A male subject aged 78 · a dermatoscopic image of a skin lesion — 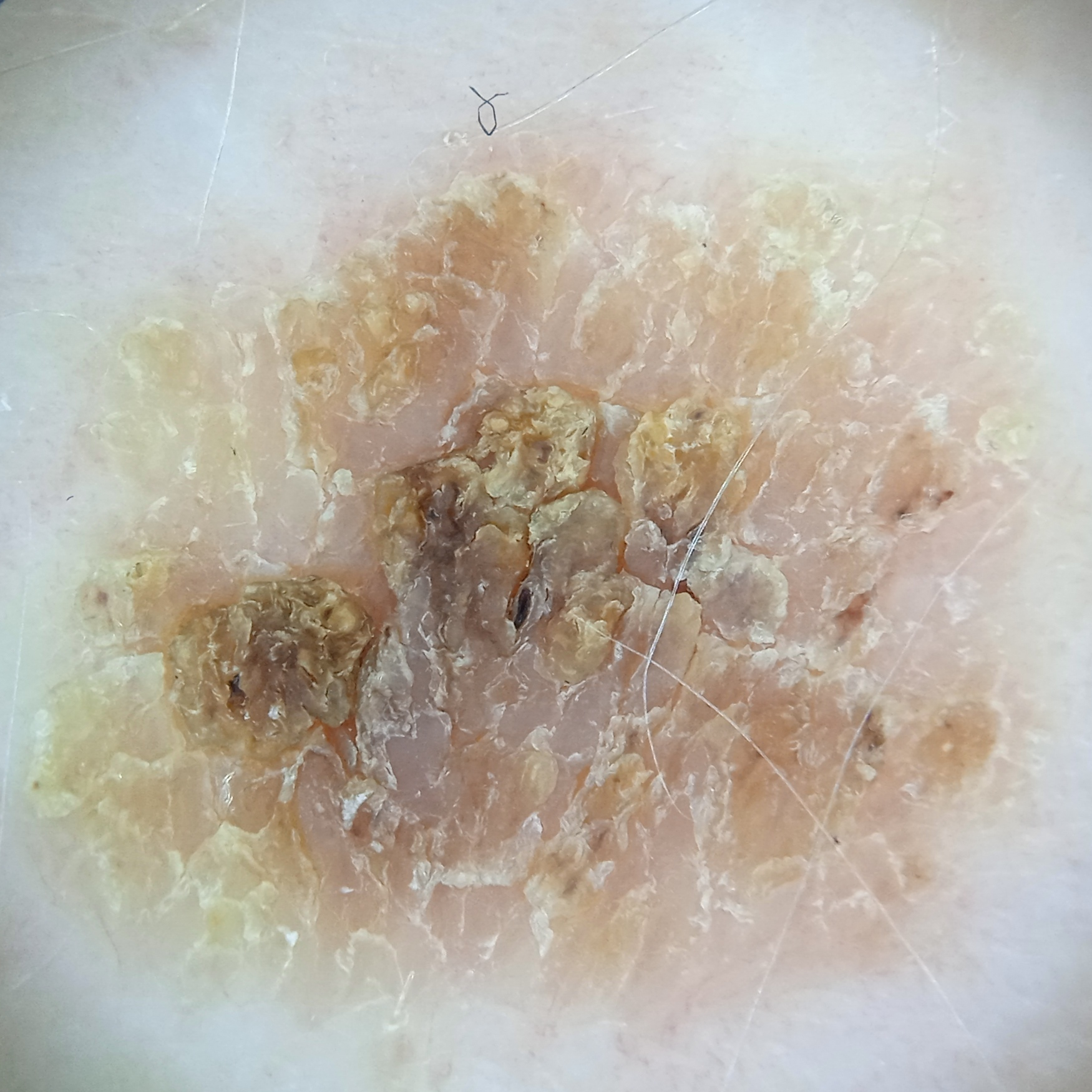The lesion involves the back. The lesion is about 11 mm across. The lesion was assessed as a seborrheic keratosis.